This is a close-up image.
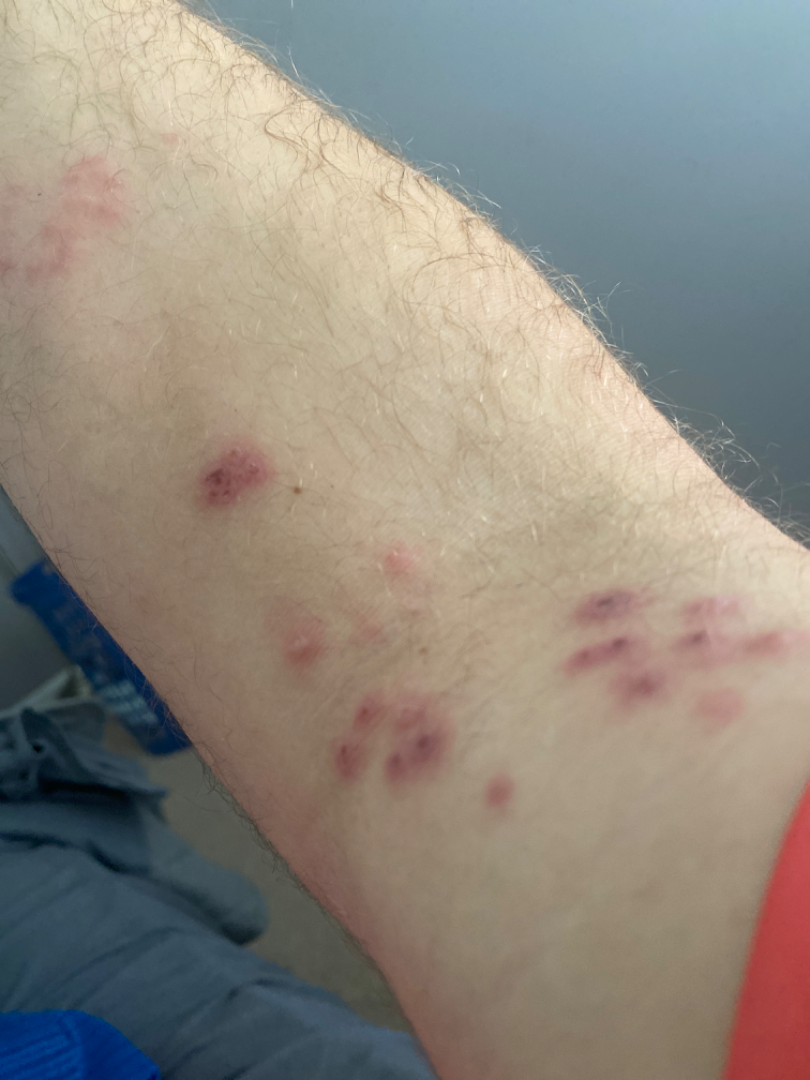Q: Fitzpatrick or Monk tone?
A: Fitzpatrick phototype III
Q: What conditions are considered?
A: most consistent with Herpes Zoster